A dermoscopic photograph of a skin lesion.
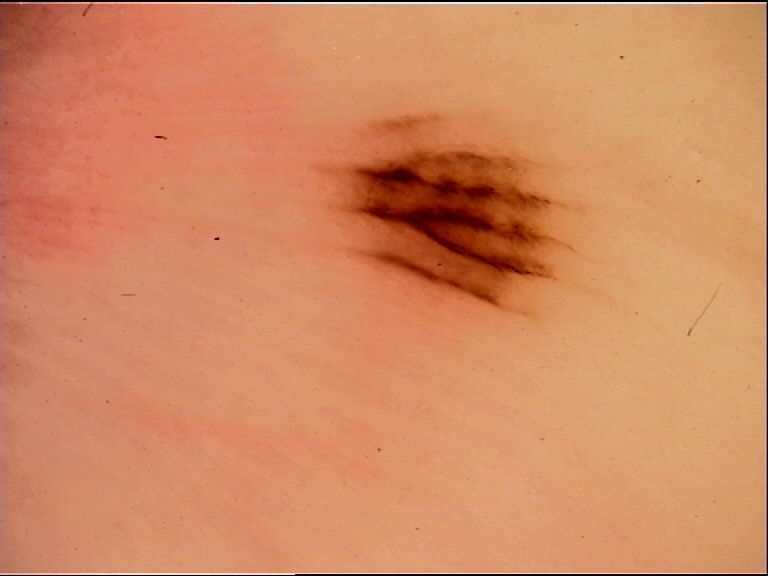Consistent with an acral junctional nevus.